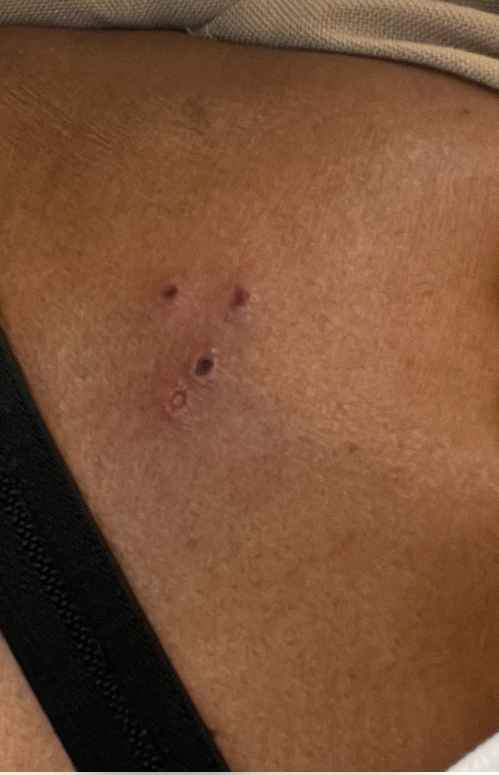A close-up photograph.
The patient indicates the condition has been present for less than one week.
No relevant lesion symptoms reported.
Texture is reported as flat.
The subject is 50–59, female.
Eczema (0.67); Herpes Simplex (0.33).